Texture is reported as raised or bumpy. Reported lesion symptoms include enlargement, burning, itching and bothersome appearance. No relevant systemic symptoms. This image was taken at a distance. The lesion involves the leg. Female contributor, age 18–29. The patient considered this a rash. The condition has been present for less than one week:
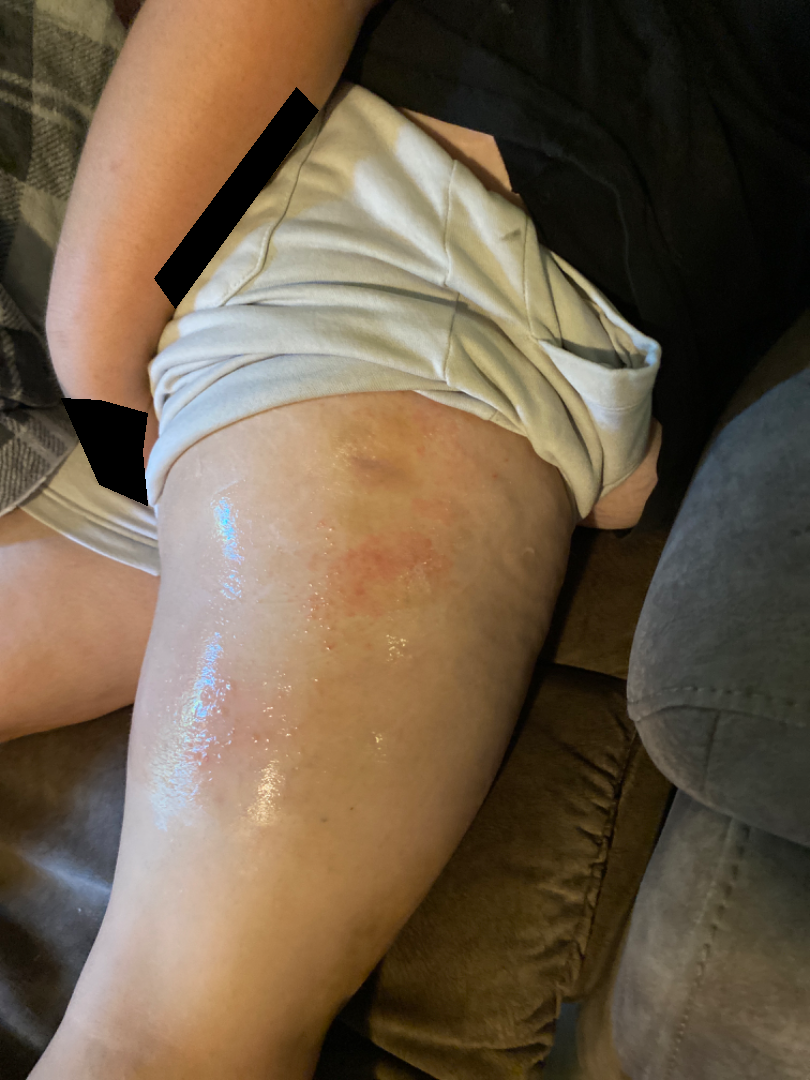The primary impression is Eczema; possibly Contact dermatitis; a remote consideration is Allergic Contact Dermatitis; less probable is Darier's disease; less likely is Hailey Hailey disease.